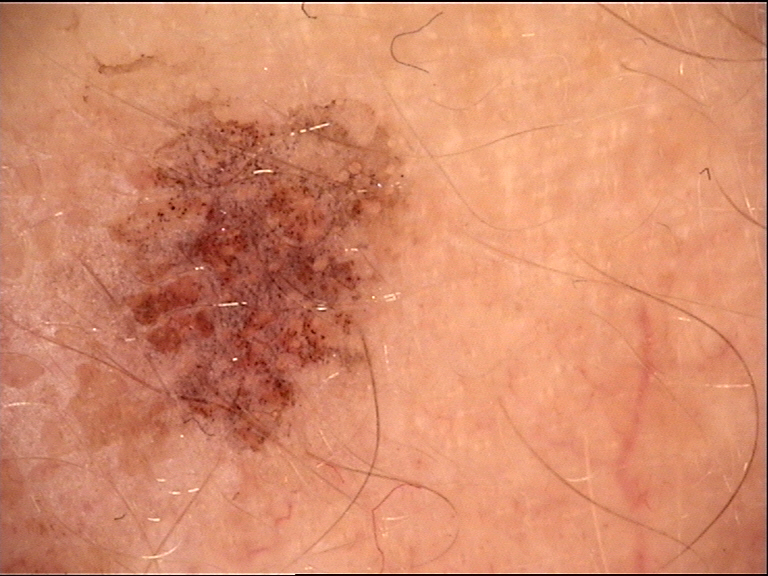Consistent with a lichenoid keratosis.